A skin lesion imaged with a dermatoscope:
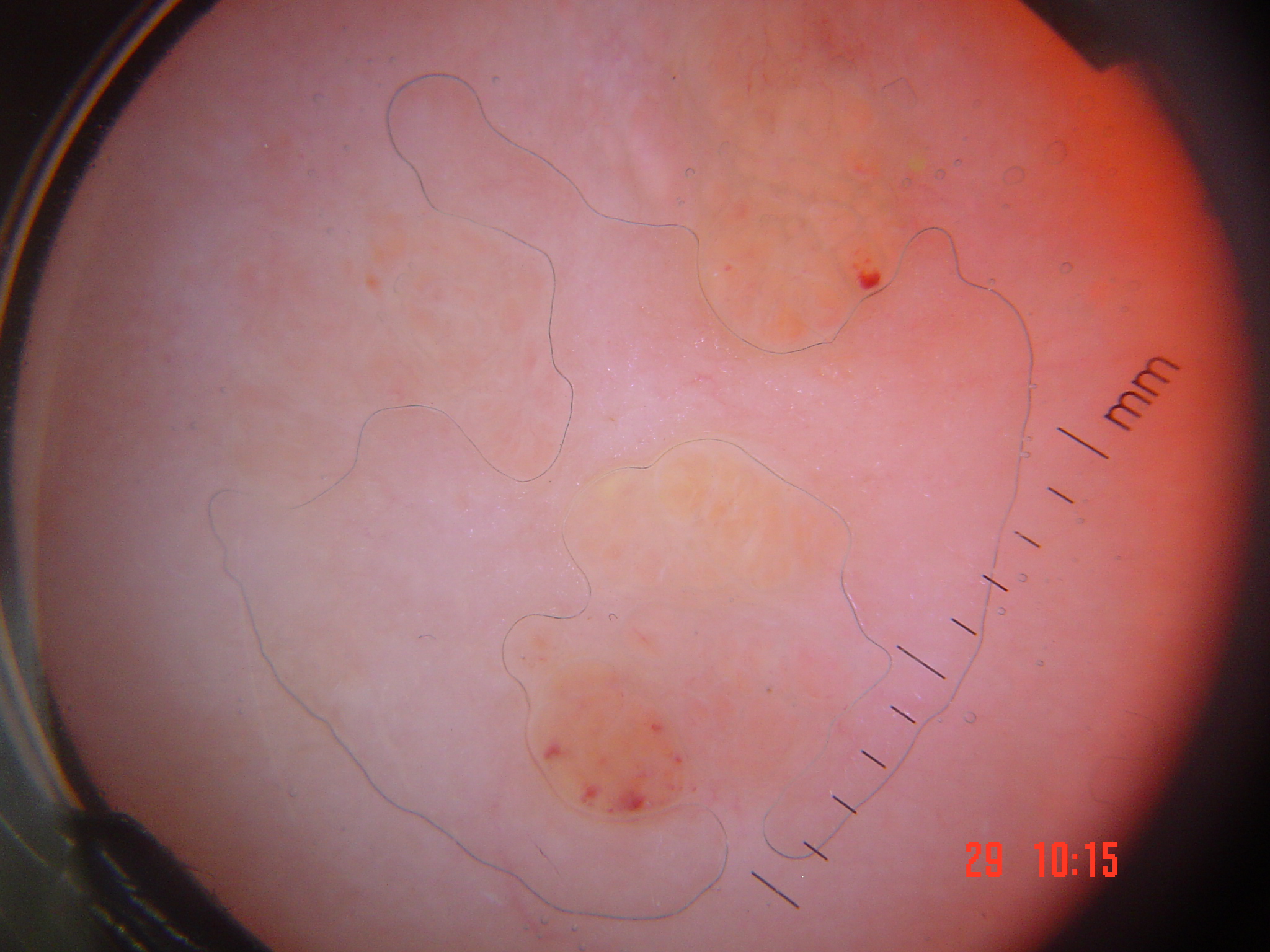| field | value |
|---|---|
| diagnosis | lymphangioma (expert consensus) |